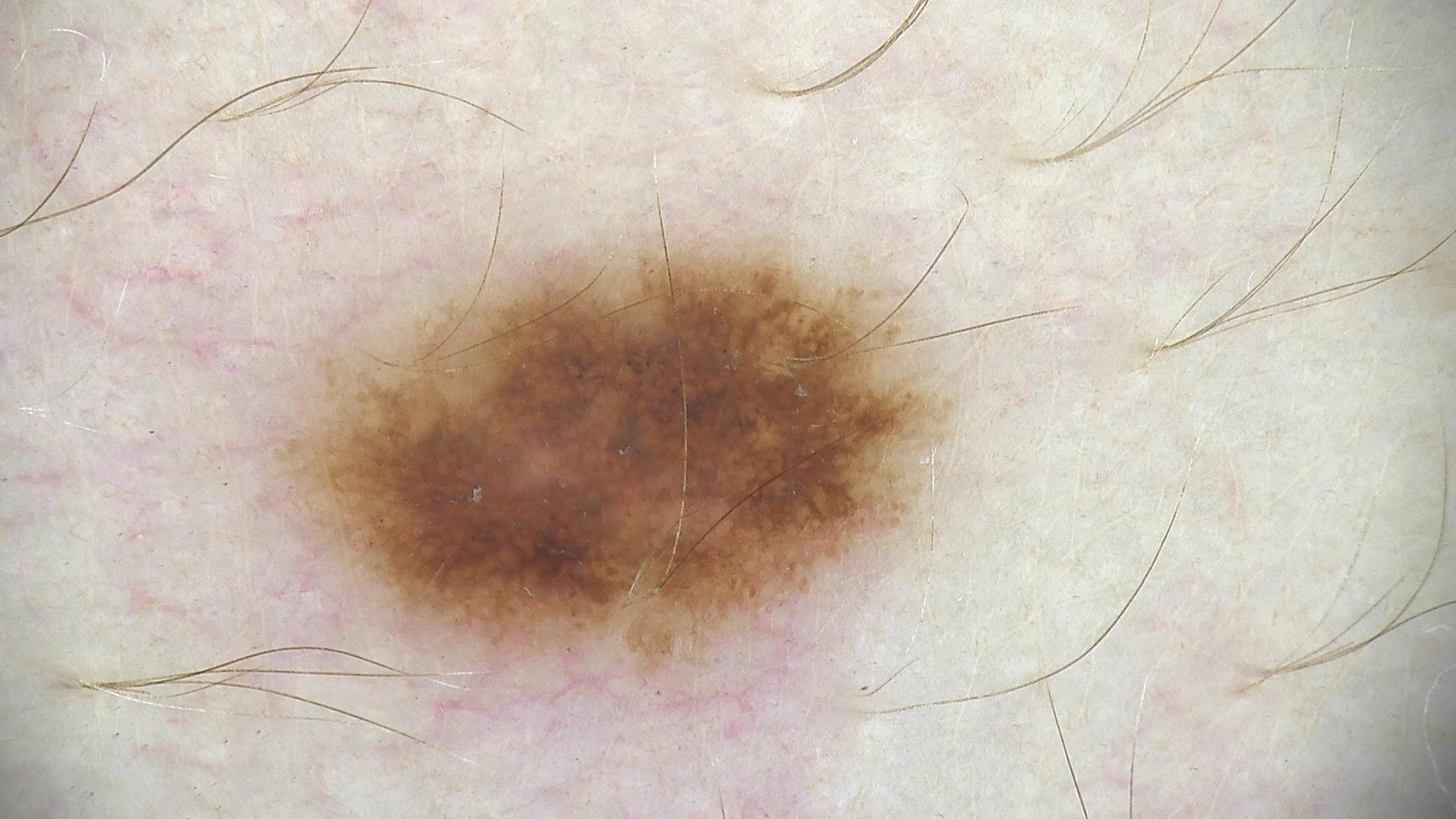Q: What is this lesion?
A: dysplastic junctional nevus (expert consensus)